A dermatoscopic image of a skin lesion.
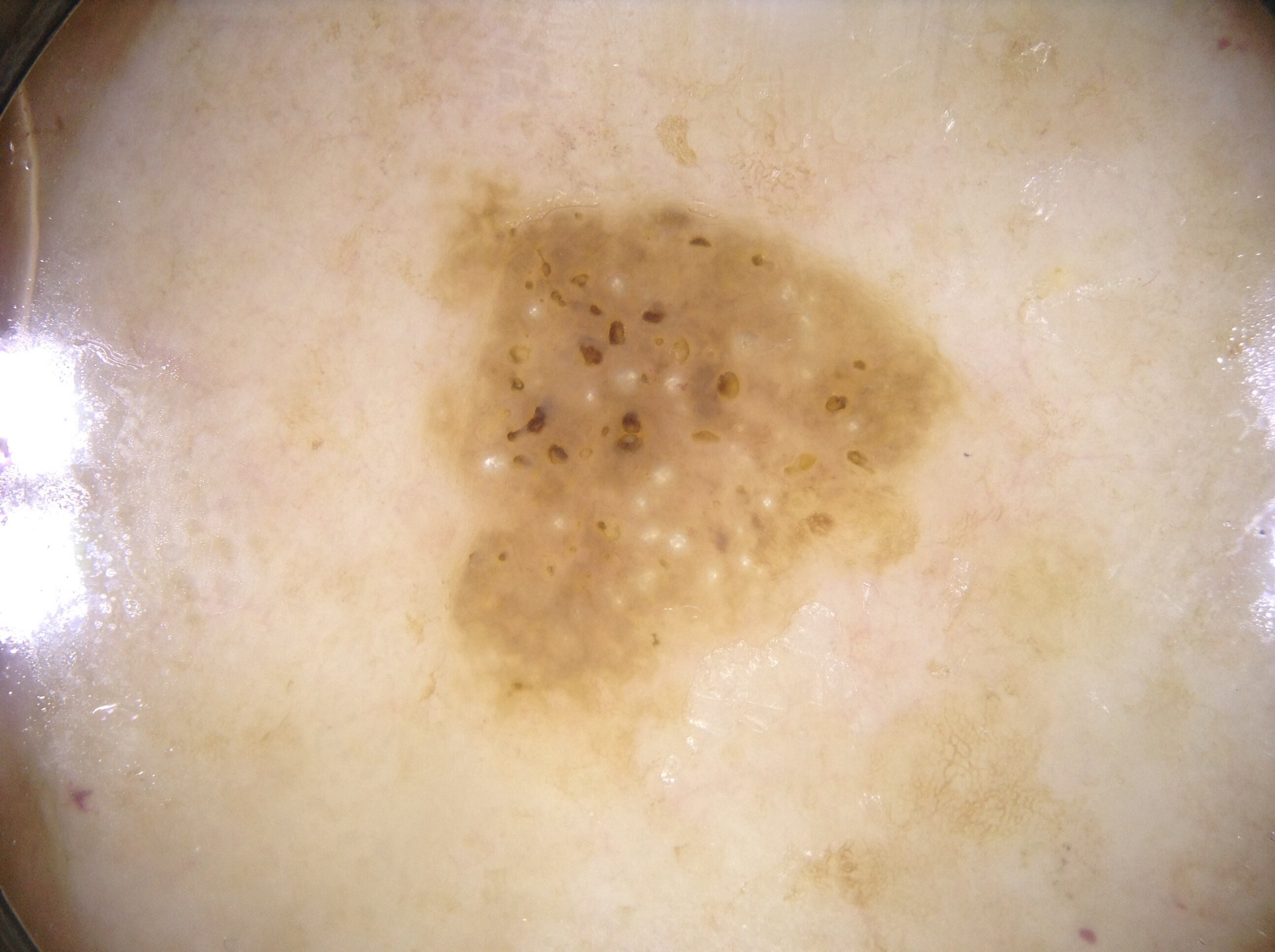  lesion_location:
    bbox_xyxy:
      - 439
      - 186
      - 956
      - 714
  diagnosis:
    name: seborrheic keratosis
    malignancy: benign
    lineage: keratinocytic
    provenance: clinical